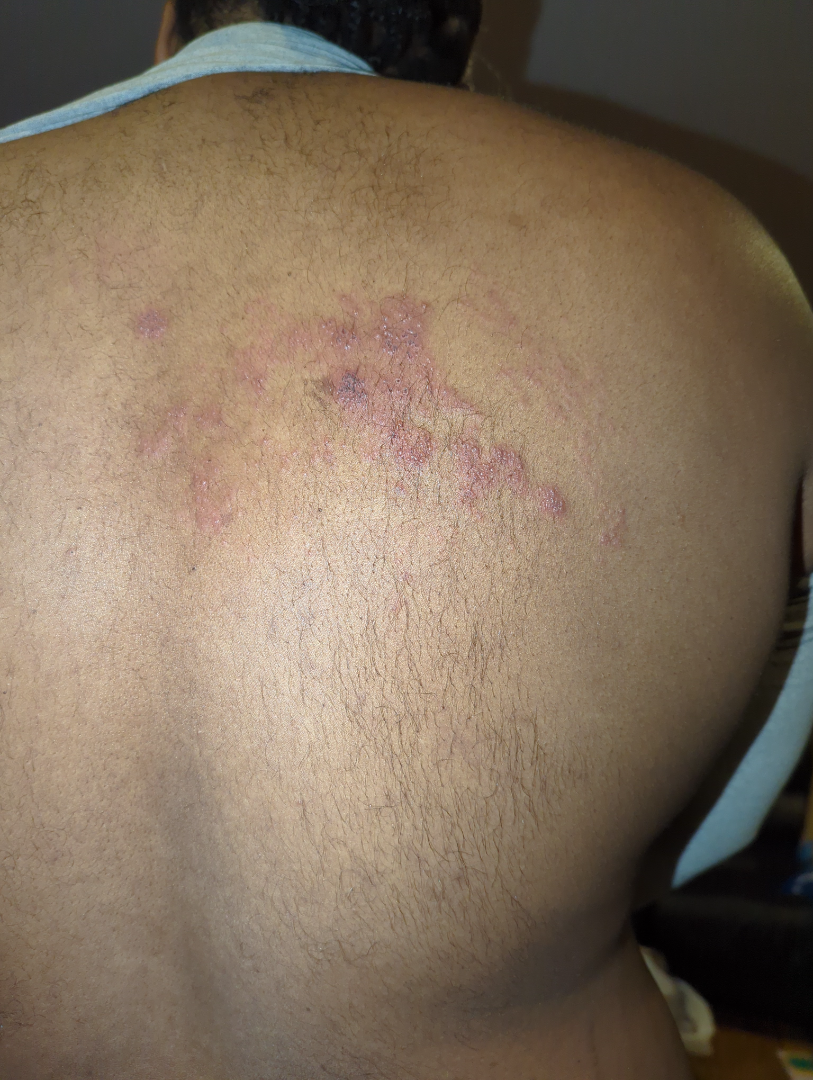image framing = at a distance, location = back of the torso, clinical impression = in keeping with Herpes Zoster.